No relevant systemic symptoms. The affected area is the front of the torso. Skin tone: non-clinician graders estimated 2 on the Monk skin tone scale. The patient notes the lesion is raised or bumpy. The contributor is female. The photo was captured at an angle. The patient notes the condition has been present for one to four weeks.
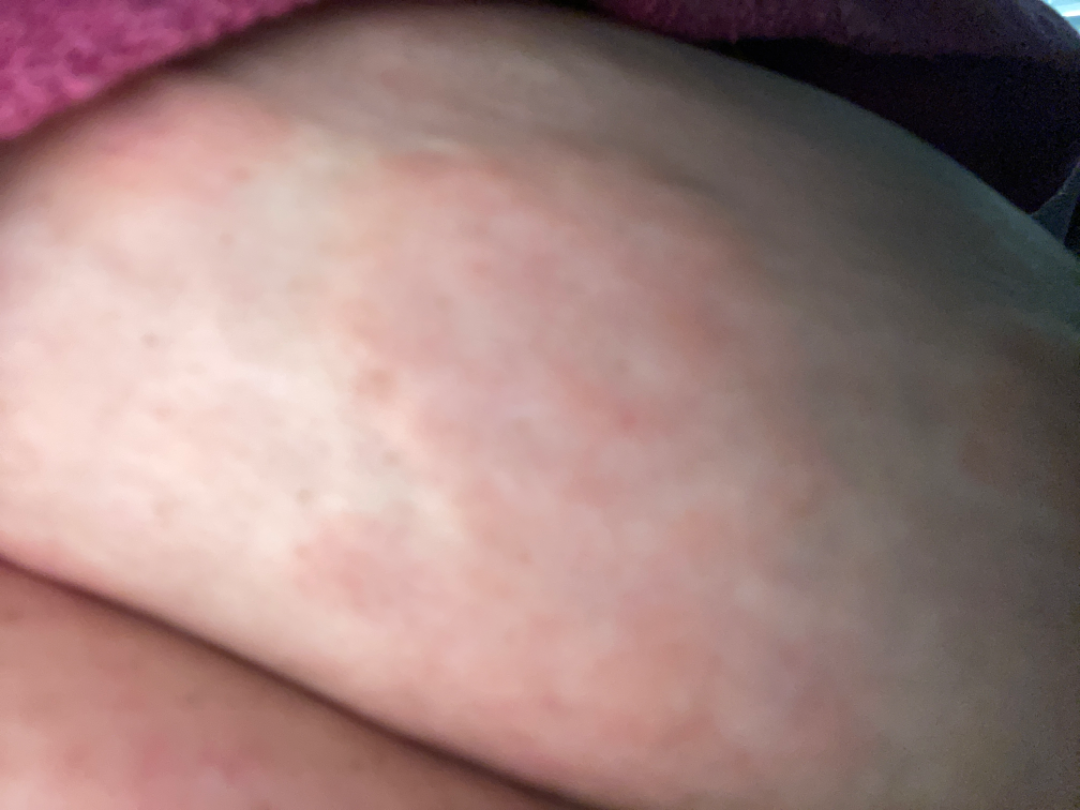assessment: not assessable.